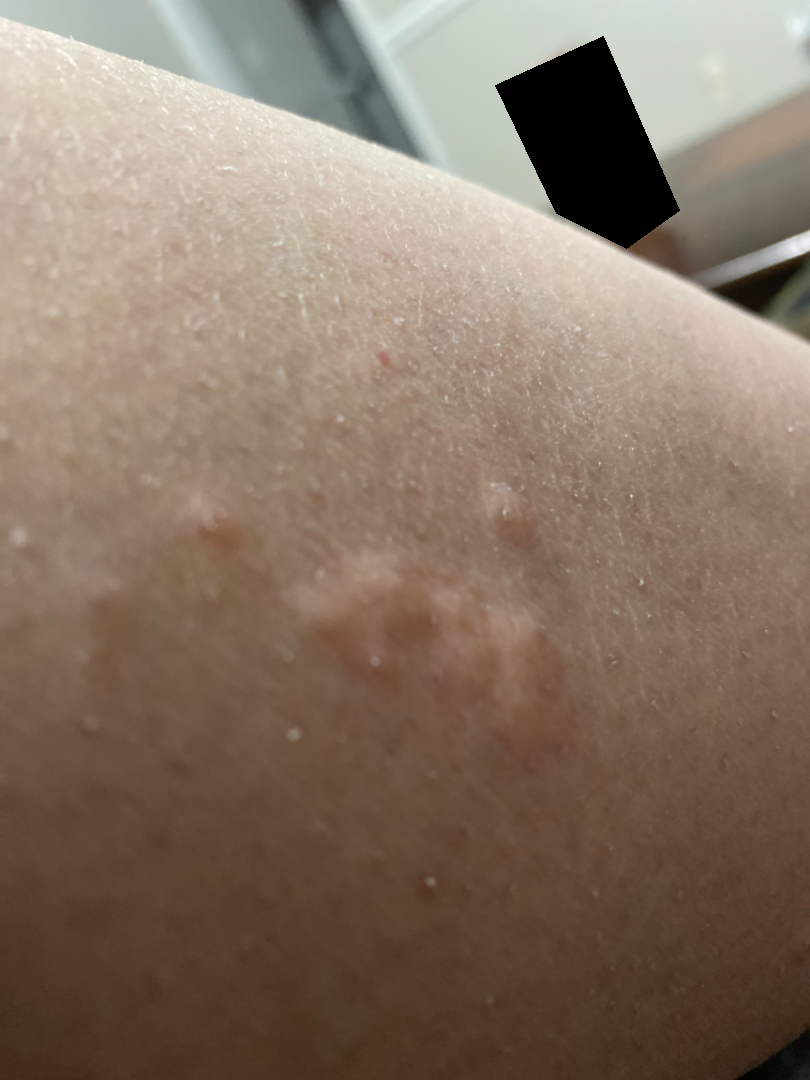| feature | finding |
|---|---|
| assessment | unable to determine |
| patient-reported symptoms | itching |
| photo taken | close-up |
| contributor | female, age 50–59 |
| surface texture | raised or bumpy |
| self-categorized as | a rash |
| onset | about one day |
| other reported symptoms | none reported |
| anatomic site | leg |